A clinical close-up photograph of a skin lesion; Fitzpatrick skin type II; by history, prior skin cancer (patient or family), no prior malignancy (patient or family), and no pesticide exposure.
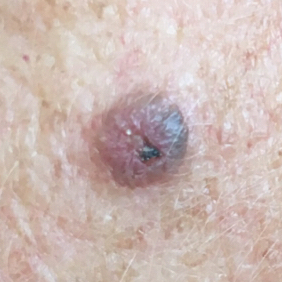The lesion is located on the face. The lesion is roughly 5 by 5 mm. The patient reports that the lesion has grown, itches, and has bled. The biopsy diagnosis was a seborrheic keratosis.